A dermoscopy image of a single skin lesion. A female subject about 55 years old — 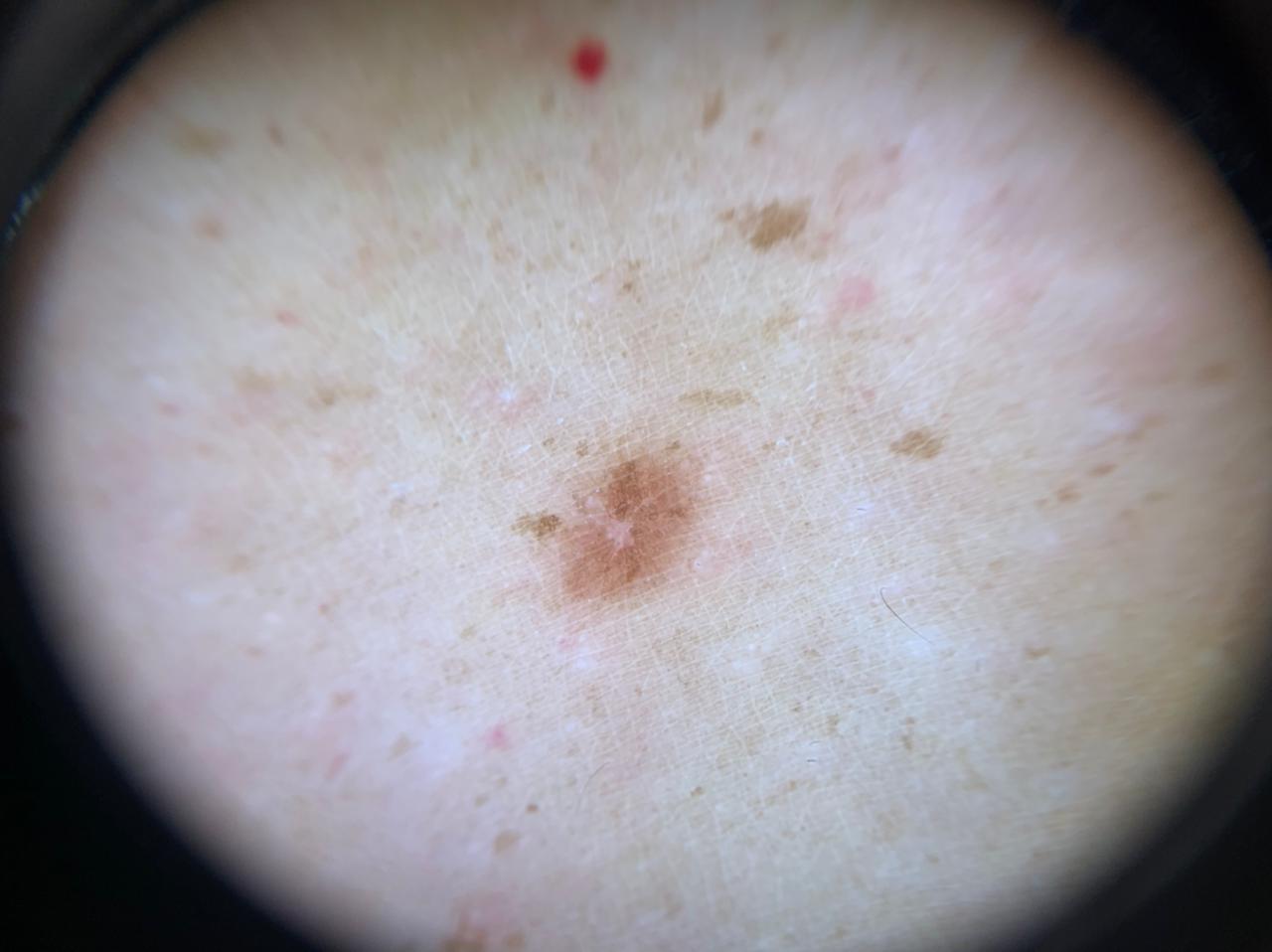Clinical context:
The lesion was found on a lower extremity.
Conclusion:
Clinically diagnosed as a dermatofibroma.